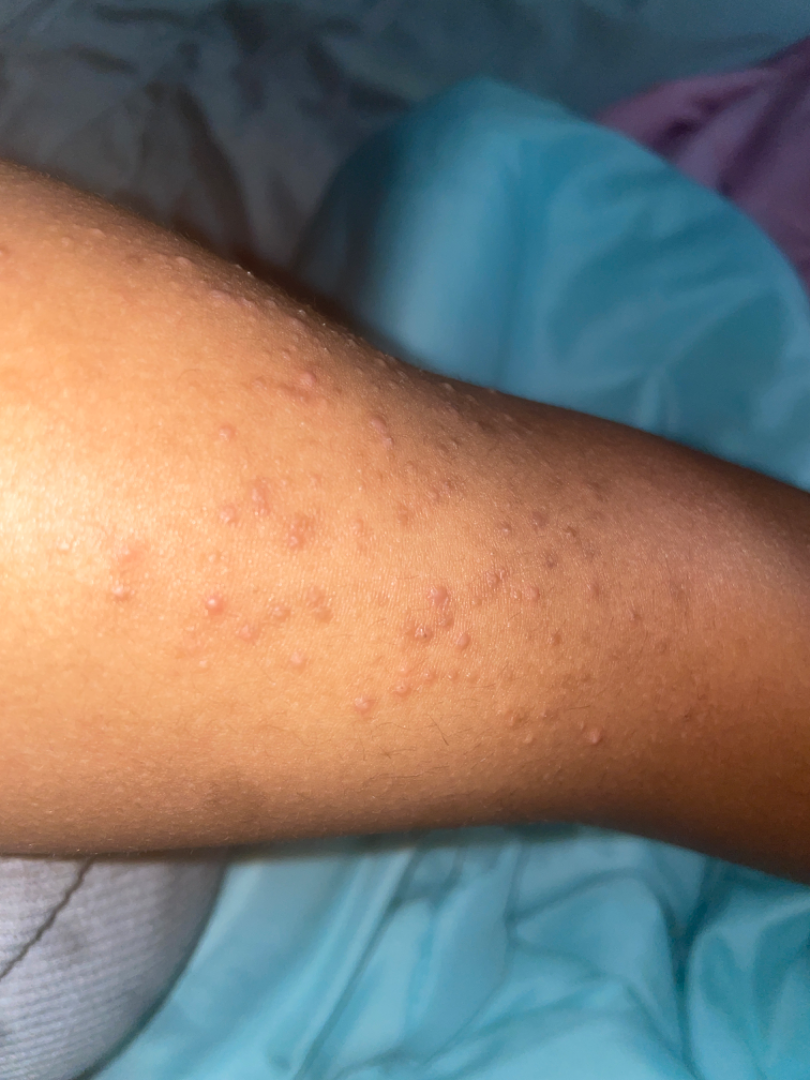Reviewed remotely by one dermatologist: the impression was split between Folliculitis and Chronic dermatitis, NOS.